Self-categorized by the patient as a rash; no constitutional symptoms were reported; the lesion is associated with itching; the lesion involves the head or neck, arm, leg and back of the torso; present for about one day; the lesion is described as raised or bumpy and fluid-filled; this image was taken at a distance:
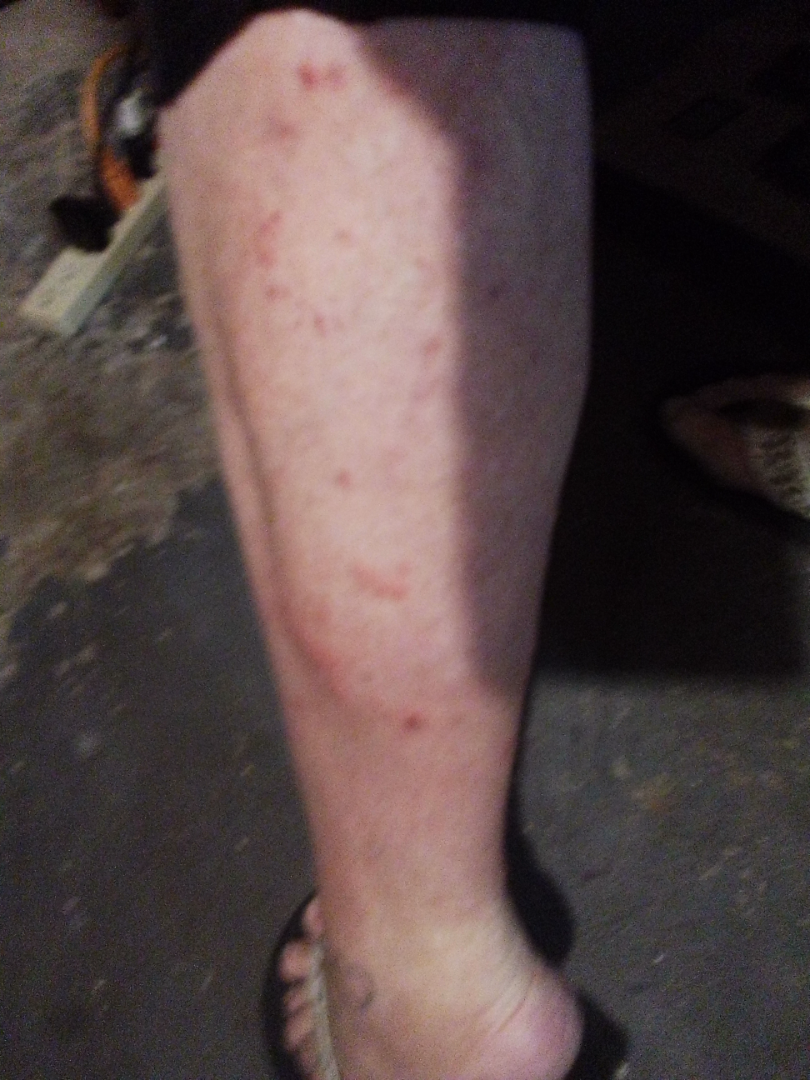The image was not sufficient for the reviewer to characterize the skin condition.